A dermoscopy image of a single skin lesion.
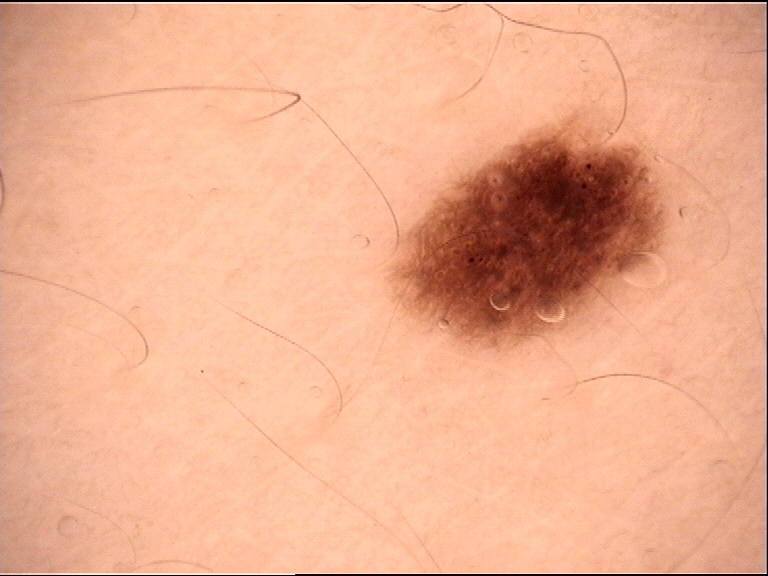label = dysplastic junctional nevus (expert consensus).